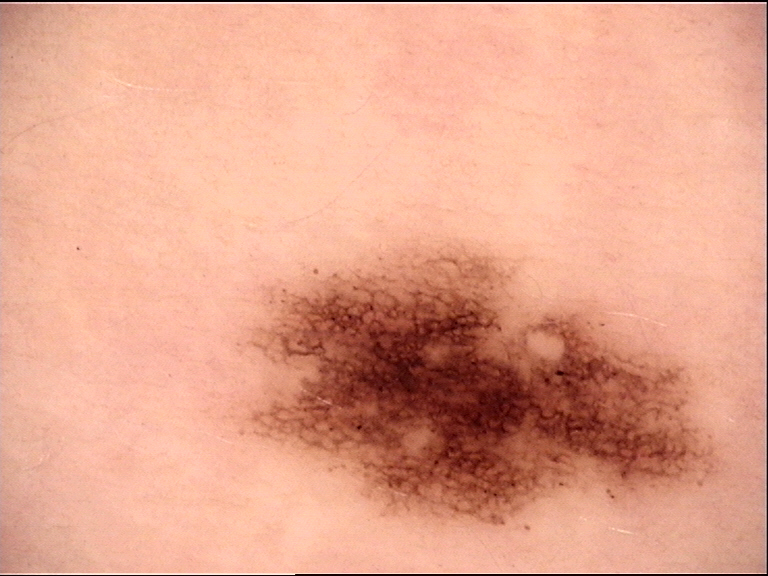Summary:
A dermoscopy image of a single skin lesion.
Conclusion:
The diagnostic label was a benign lesion — a dysplastic junctional nevus.